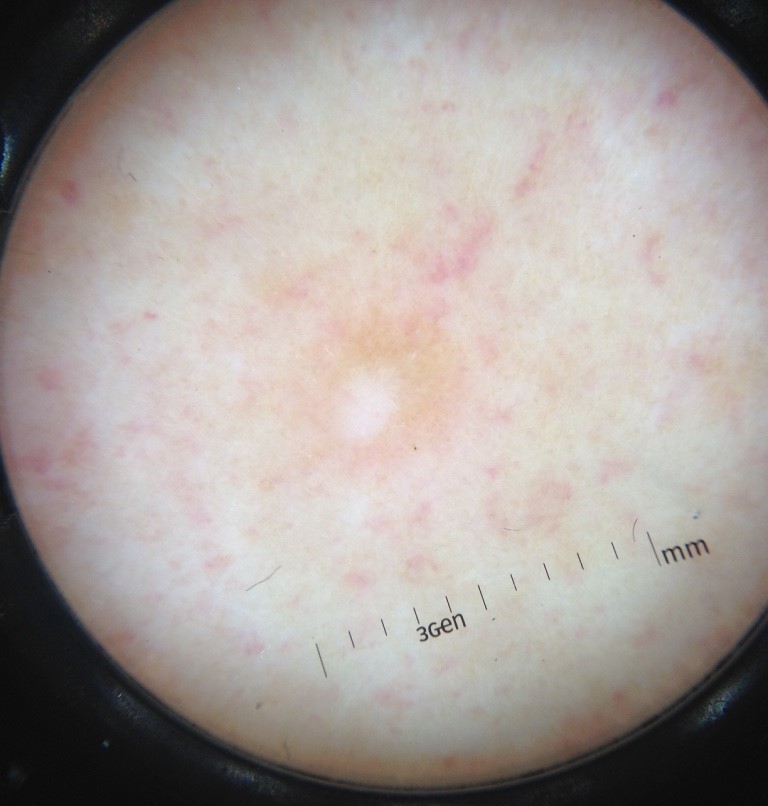lesion type — fibro-histiocytic; assessment — dermatofibroma (expert consensus).